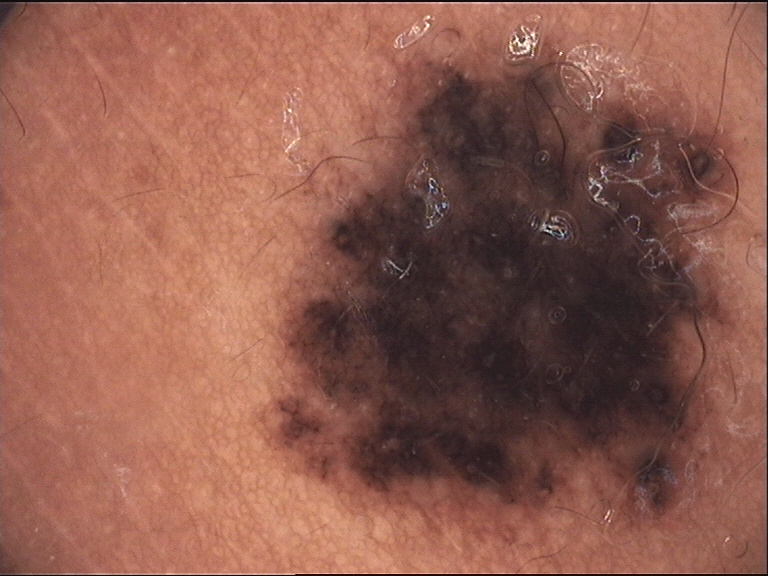diagnosis = congenital dysplastic compound nevus (expert consensus).